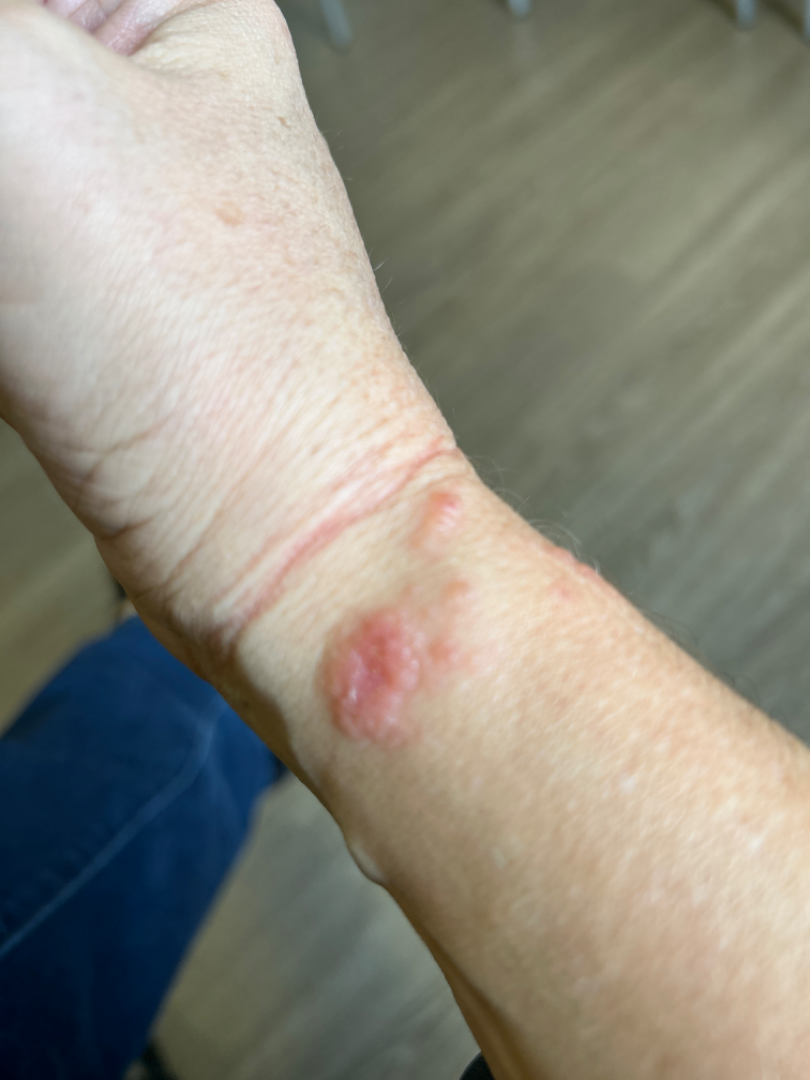assessment = indeterminate from the photograph | patient's own categorization = a rash | view = close-up | reported symptoms = enlargement, itching and bothersome appearance | onset = less than one week | texture = rough or flaky and raised or bumpy | location = arm | skin tone = Fitzpatrick skin type II; lay graders estimated Monk Skin Tone 2 or 3 (two reviewer pools).